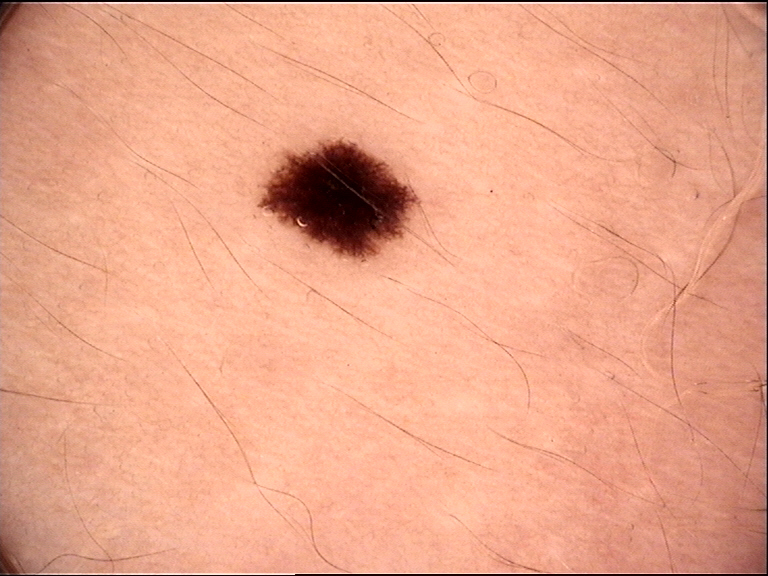diagnosis: dysplastic junctional nevus (expert consensus)